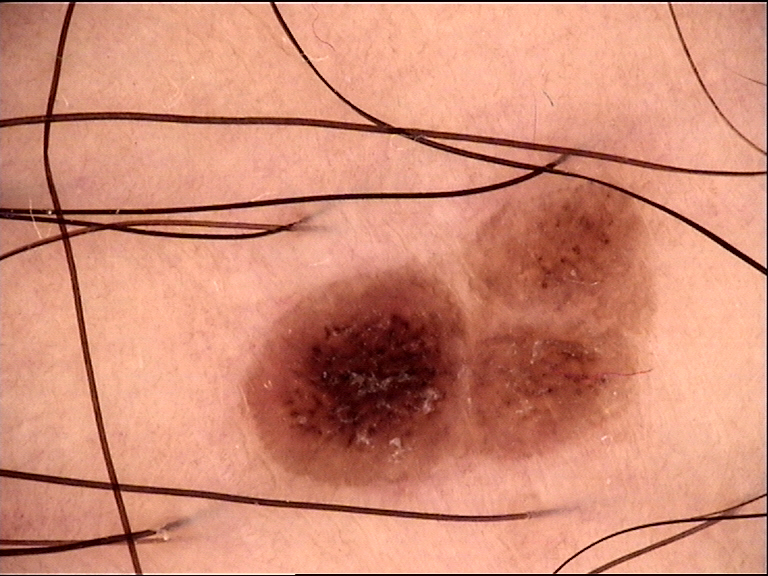The diagnosis was a dysplastic compound nevus.